The patient notes itching; the patient described the issue as a rash; an image taken at an angle; no constitutional symptoms were reported; the patient notes the condition has been present for one to four weeks; located on the back of the torso; female subject, age 50–59:
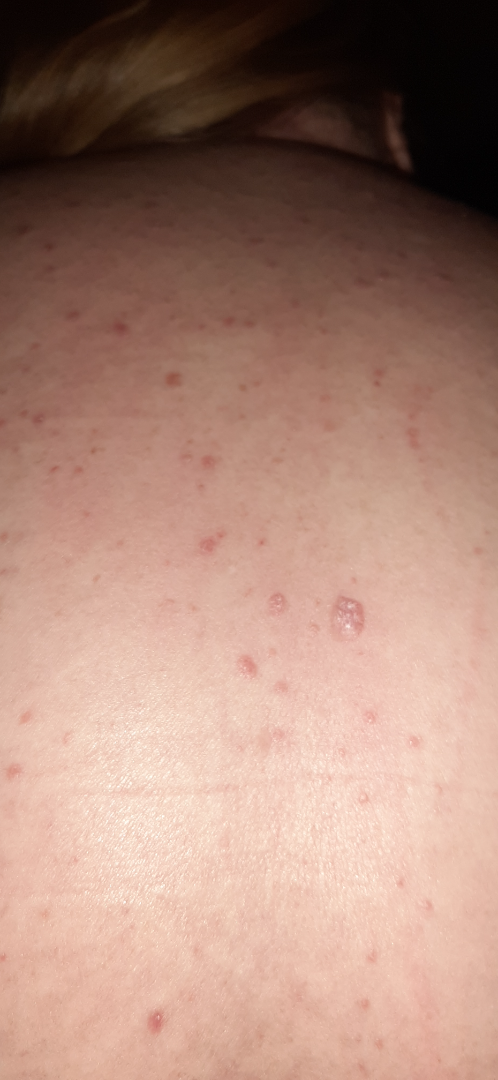The favored diagnosis is Molluscum Contagiosum; also on the differential is Verruca vulgaris; possibly SK/ISK.